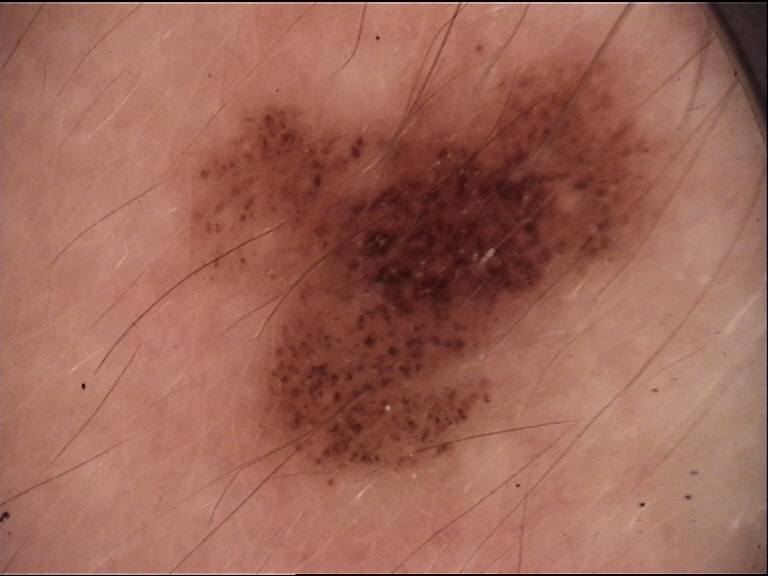class=dysplastic compound nevus (expert consensus).